The lesion involves the arm and head or neck. The photograph was taken at an angle. The contributor is a female aged 50–59 — 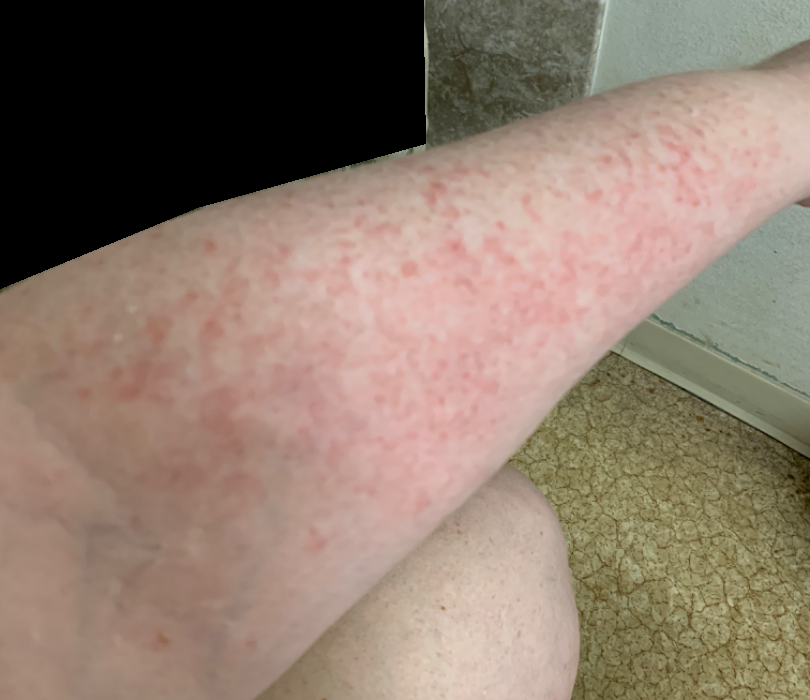The leading consideration is Drug Rash; also raised was Photodermatitis; possibly Eczema; less probable is Contact dermatitis.